Recorded as skin type II; contact-polarized dermoscopy of a skin lesion; the chart documents a previous melanoma — 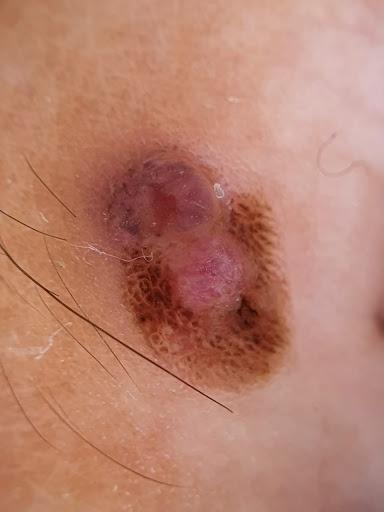<record>
<lesion_location>
<region>a lower extremity</region>
</lesion_location>
<diagnosis>
<name>Melanoma</name>
<malignancy>malignant</malignancy>
<confirmation>histopathology</confirmation>
</diagnosis>
</record>